The patient is a male aged 68-72 · a dermatoscopic image of a skin lesion — 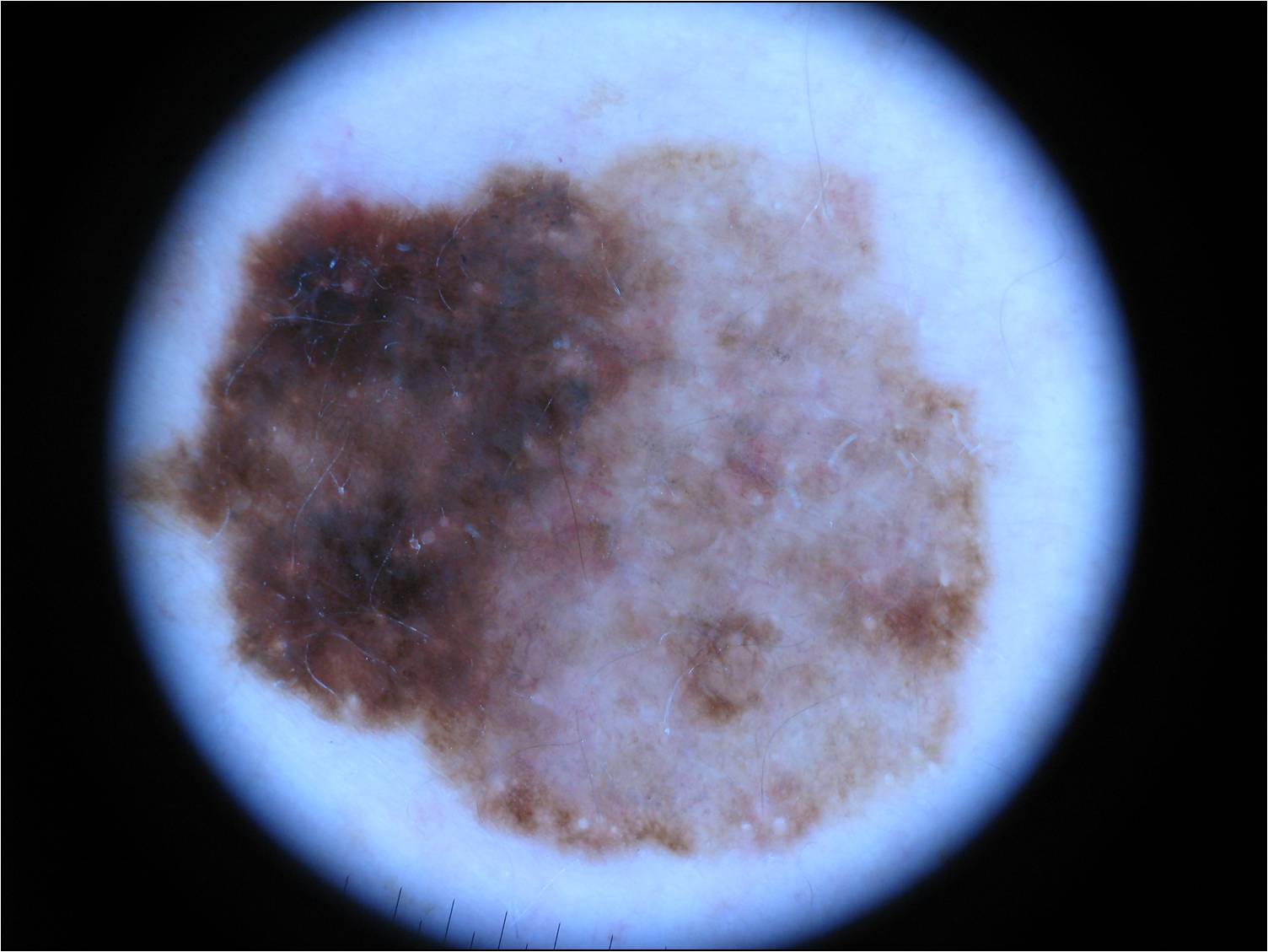  lesion_location:
    bbox_xyxy:
      - 104
      - 142
      - 1001
      - 866
  dermoscopic_features:
    present:
      - streaks
      - pigment network
    absent:
      - globules
      - negative network
      - milia-like cysts
  lesion_extent:
    approx_field_fraction_pct: 39
  diagnosis:
    name: melanoma
    malignancy: malignant
    lineage: melanocytic
    provenance: histopathology